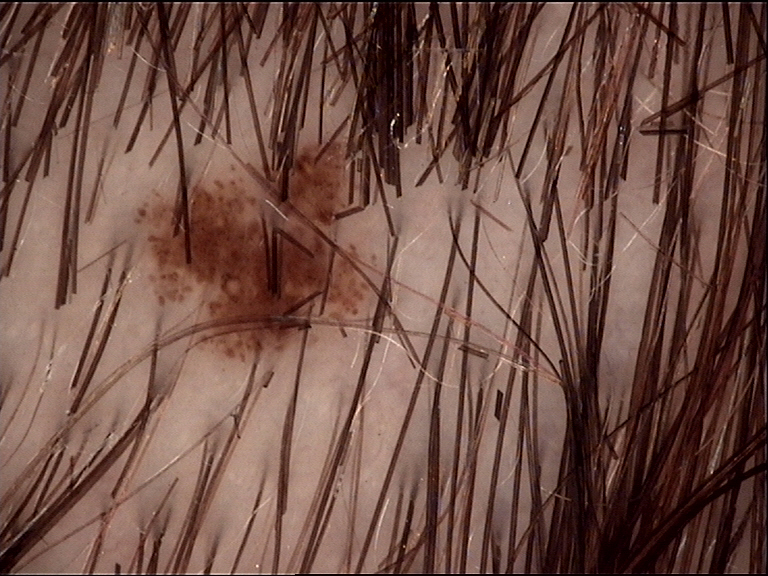diagnostic label: dysplastic junctional nevus (expert consensus).